A close-up photograph. The affected area is the leg, front of the torso and top or side of the foot.
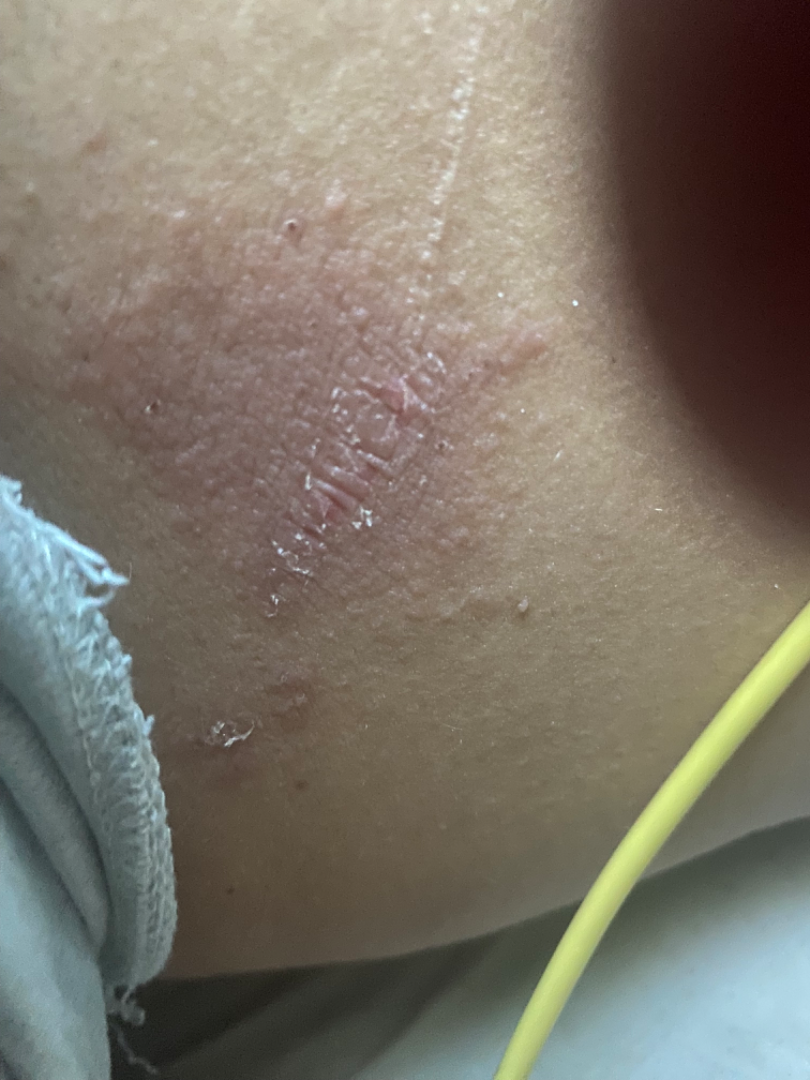Q: Could the case be diagnosed?
A: indeterminate from the photograph